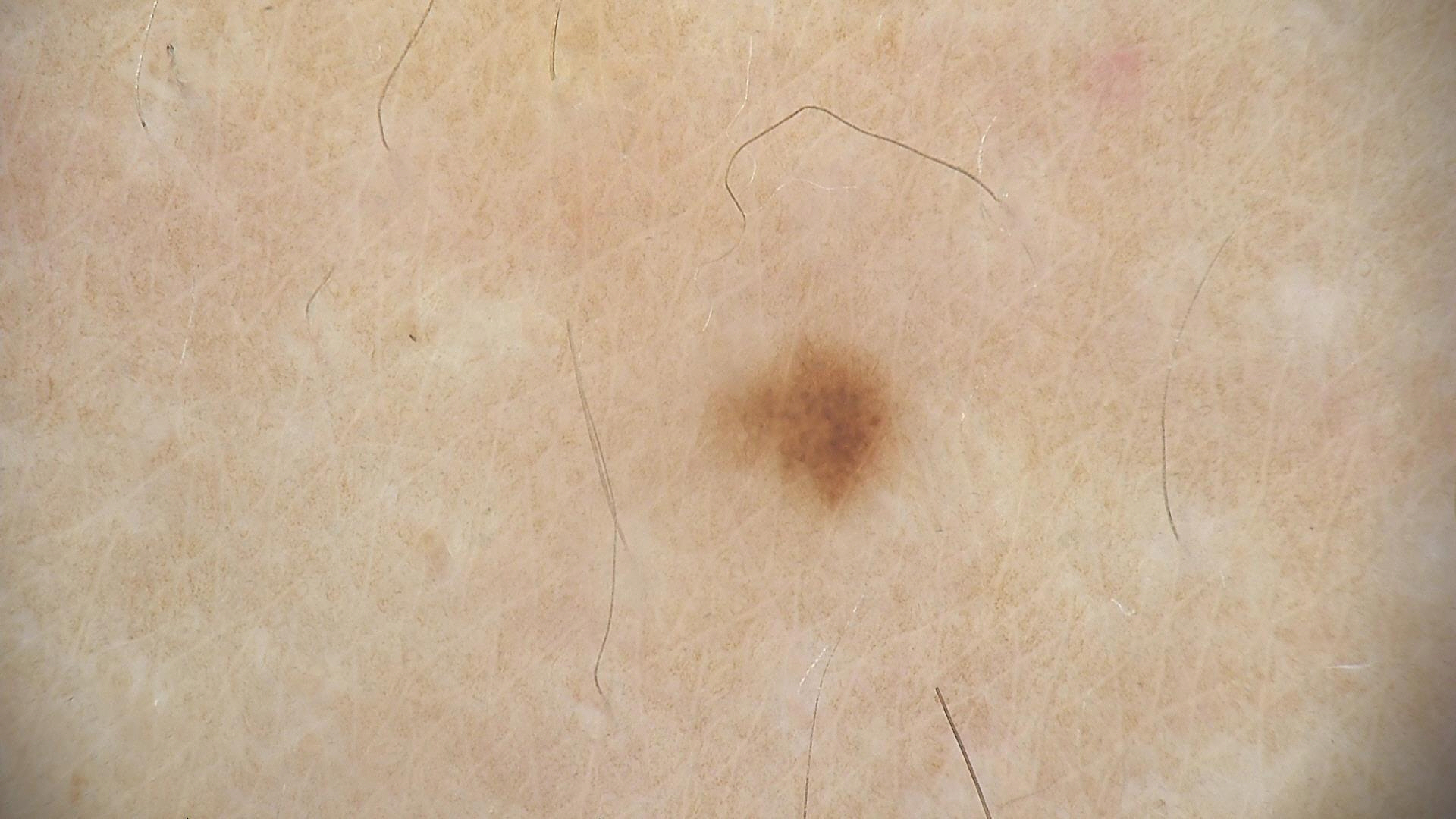A dermatoscopic image of a skin lesion.
Classified as a benign lesion — a dysplastic junctional nevus.